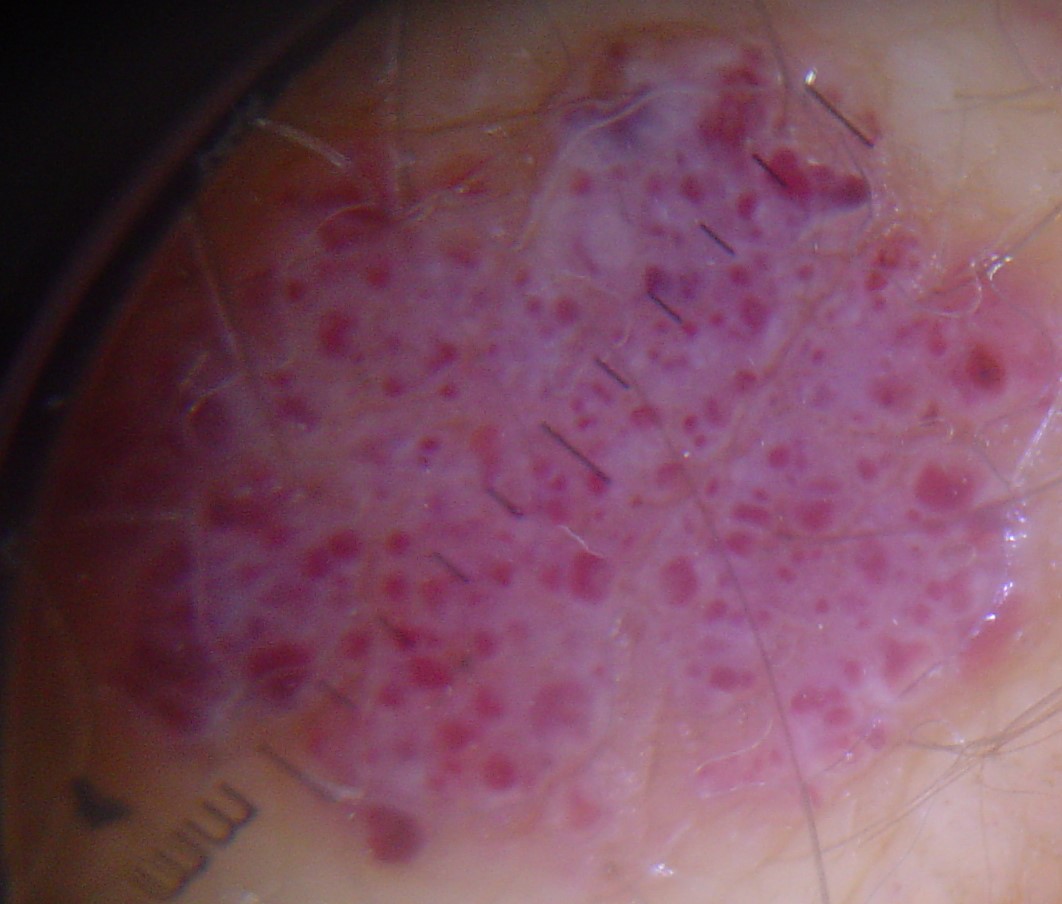Dermoscopy of a skin lesion. This is a vascular lesion. Labeled as a hemangioma.